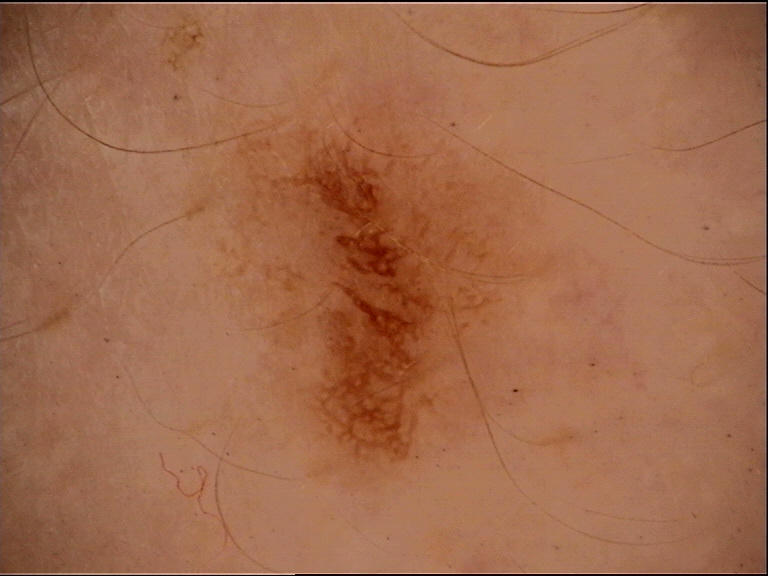The diagnostic label was a dysplastic junctional nevus.